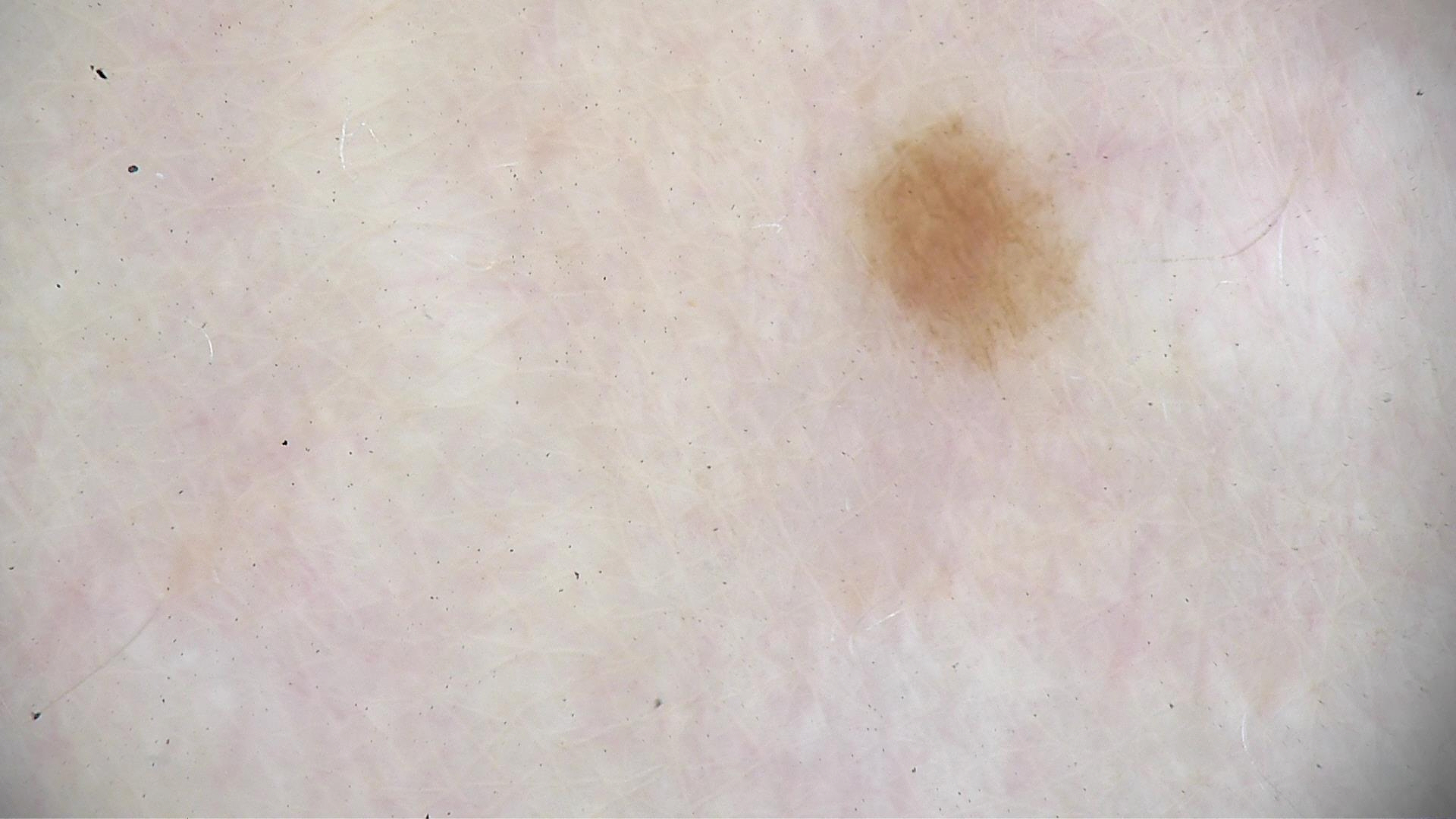image = dermatoscopy; diagnosis = dysplastic junctional nevus (expert consensus).